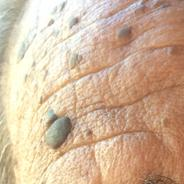A male patient in their 60s.
By history, alcohol use.
A clinical photo of a skin lesion taken with a smartphone.
The patient is Fitzpatrick skin type IV.
The lesion measures approximately 8 × 6 mm.
Per patient report, the lesion has grown and is elevated.
Consistent with a seborrheic keratosis.